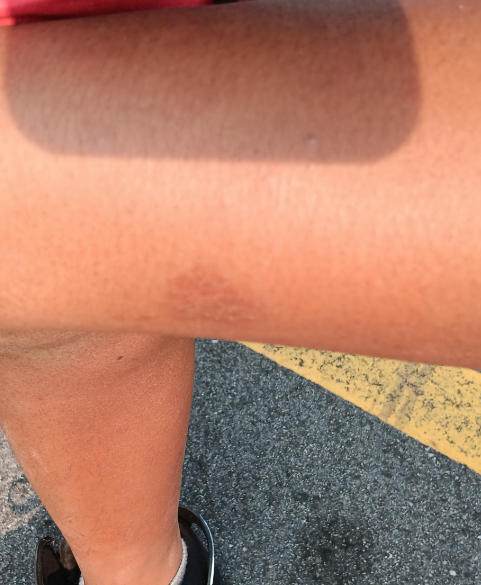<dermatology_case>
  <assessment>indeterminate from the photograph</assessment>
  <shot_type>at an angle</shot_type>
  <skin_tone>
    <fitzpatrick>V</fitzpatrick>
  </skin_tone>
</dermatology_case>